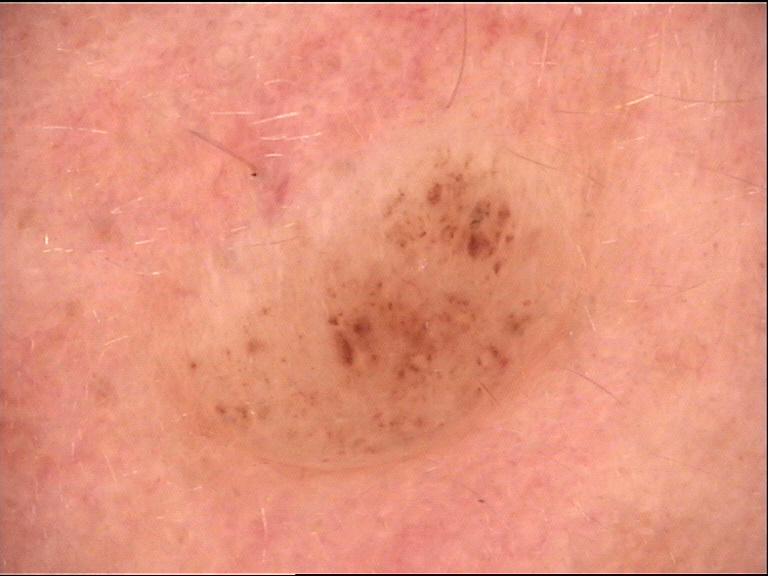The morphology is that of a banal lesion.
The diagnosis was a dermal nevus.